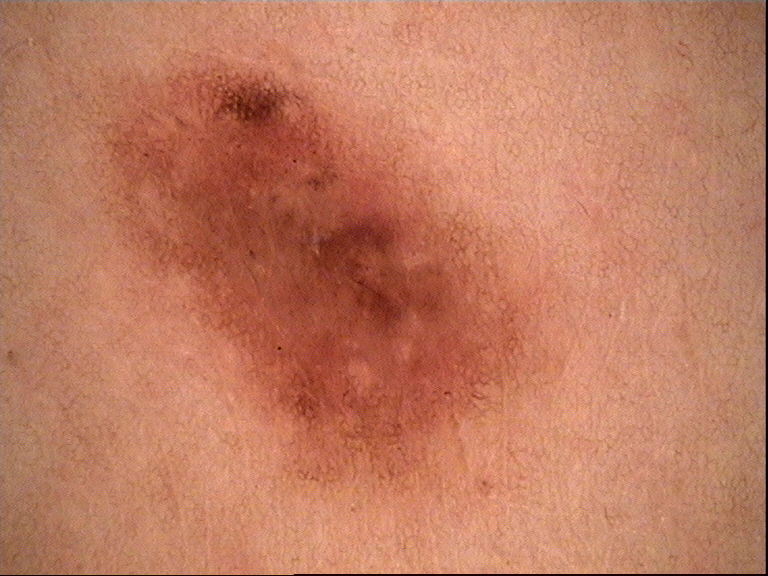| field | value |
|---|---|
| image | dermoscopy |
| diagnostic label | dysplastic compound nevus (expert consensus) |